The contributor is a female aged 18–29; the lesion is associated with bothersome appearance; the patient indicates associated fatigue; texture is reported as rough or flaky, flat and raised or bumpy; the photograph is a close-up of the affected area; located on the back of the torso, front of the torso and leg; the patient described the issue as a rash: 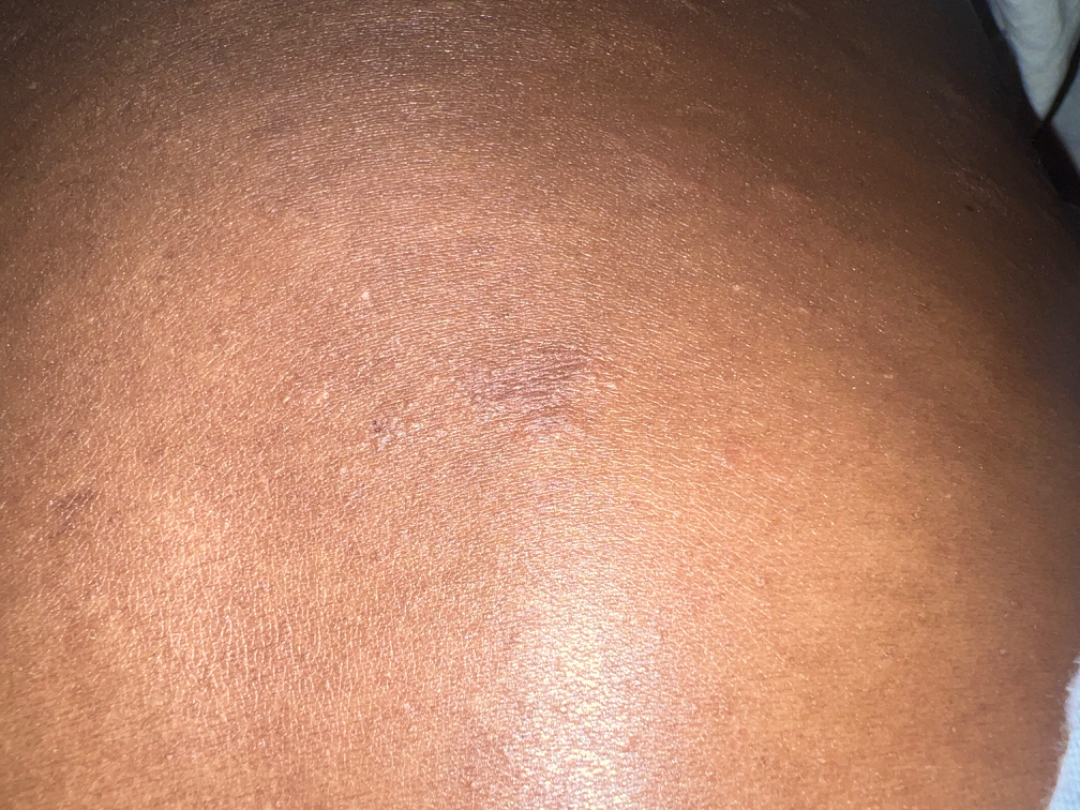On remote review of the image: the leading consideration is Pityriasis rosea.